A male subject aged 58-62 · the patient was assessed as Fitzpatrick skin type III.
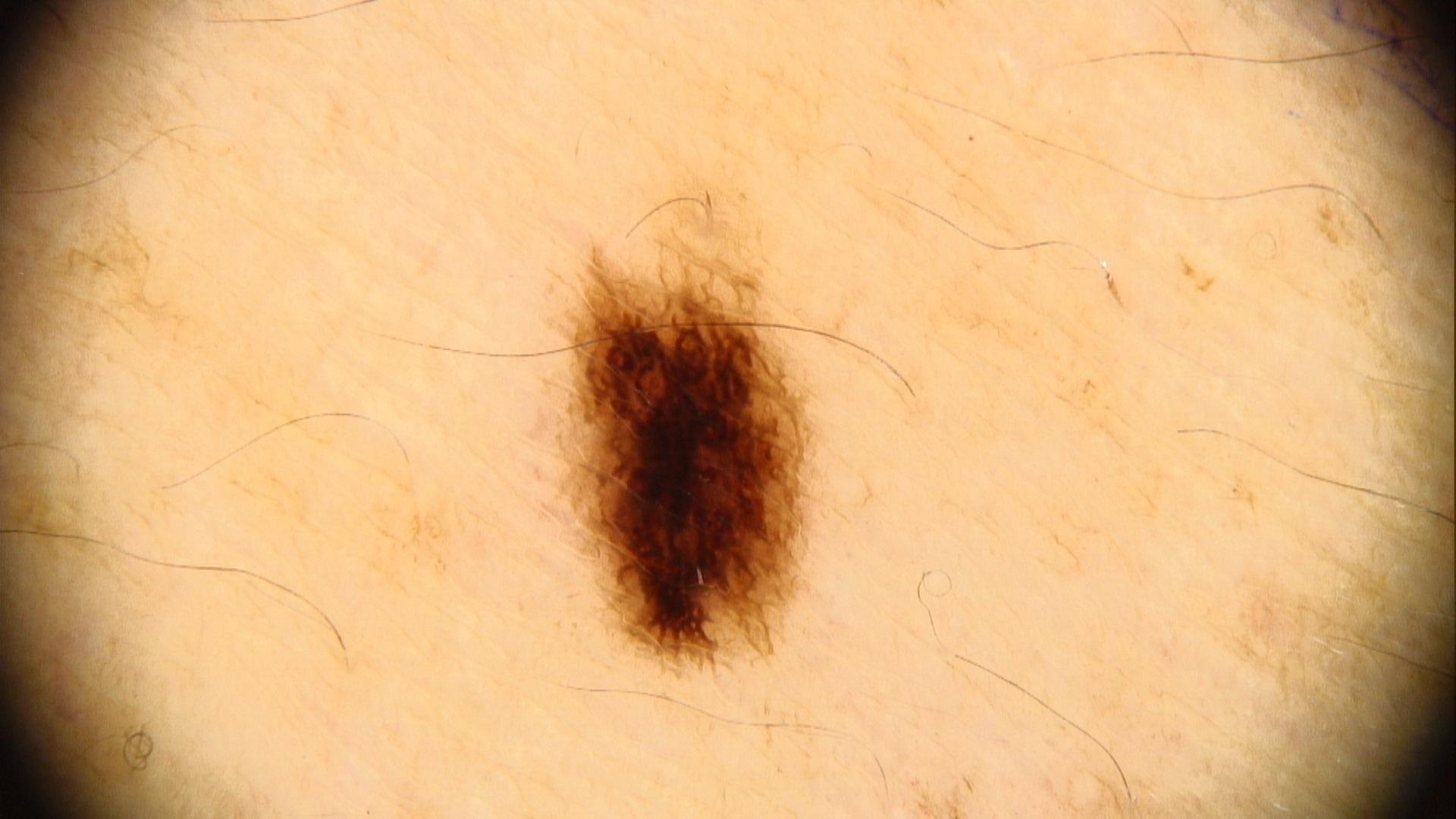Q: What is the anatomic site?
A: the posterior trunk
Q: What was the clinical impression?
A: Nevus